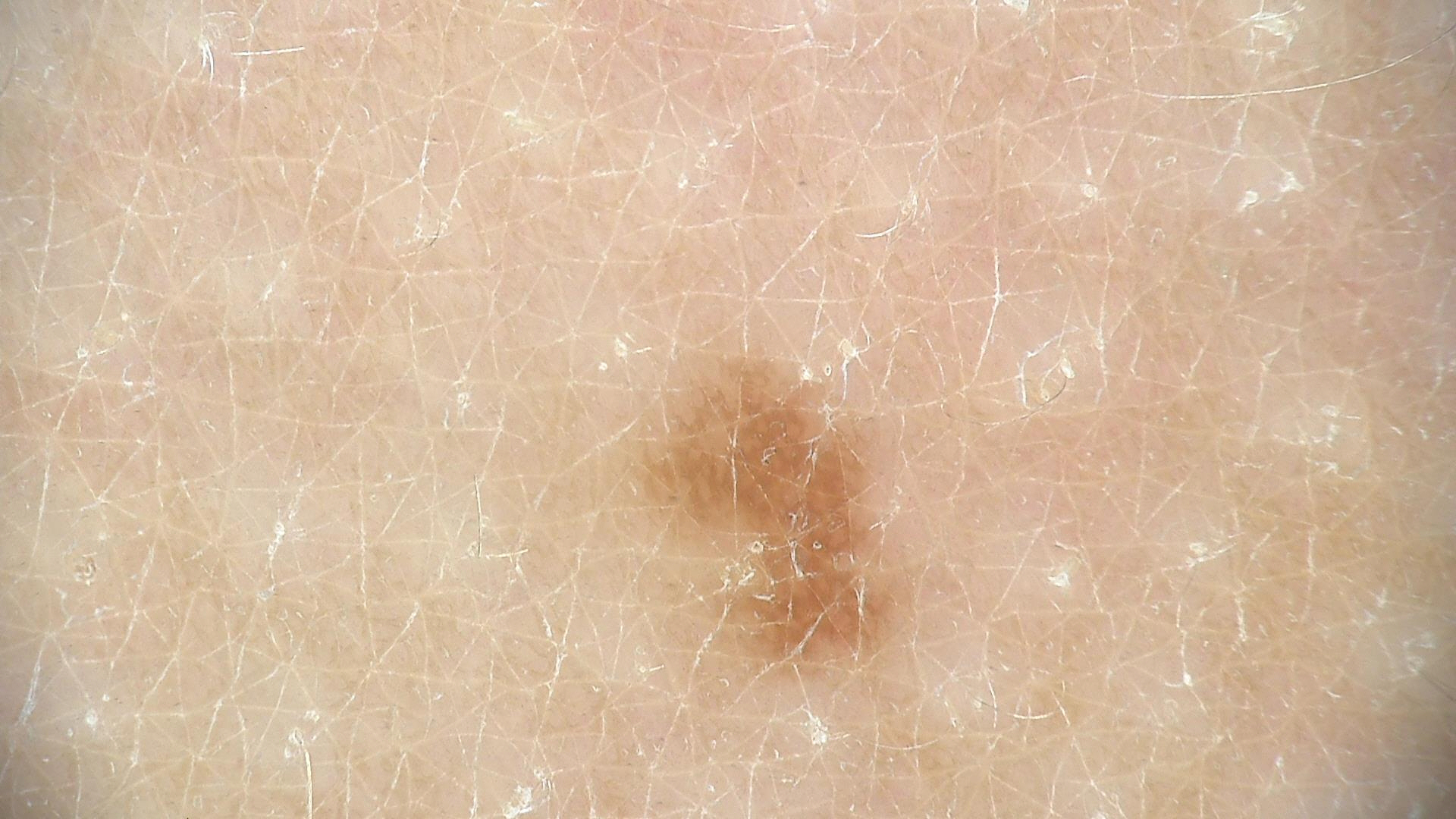Classified as a dysplastic junctional nevus.